A dermoscopic photograph of a skin lesion:
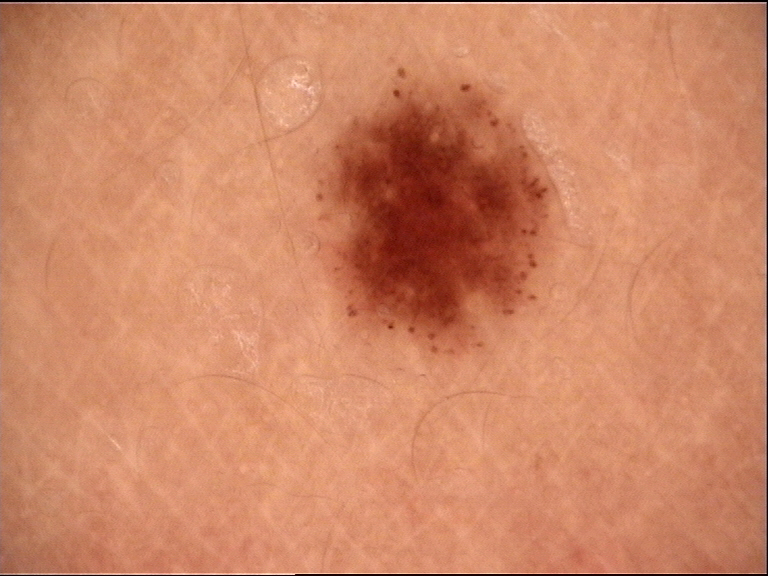The diagnostic label was a dysplastic junctional nevus.